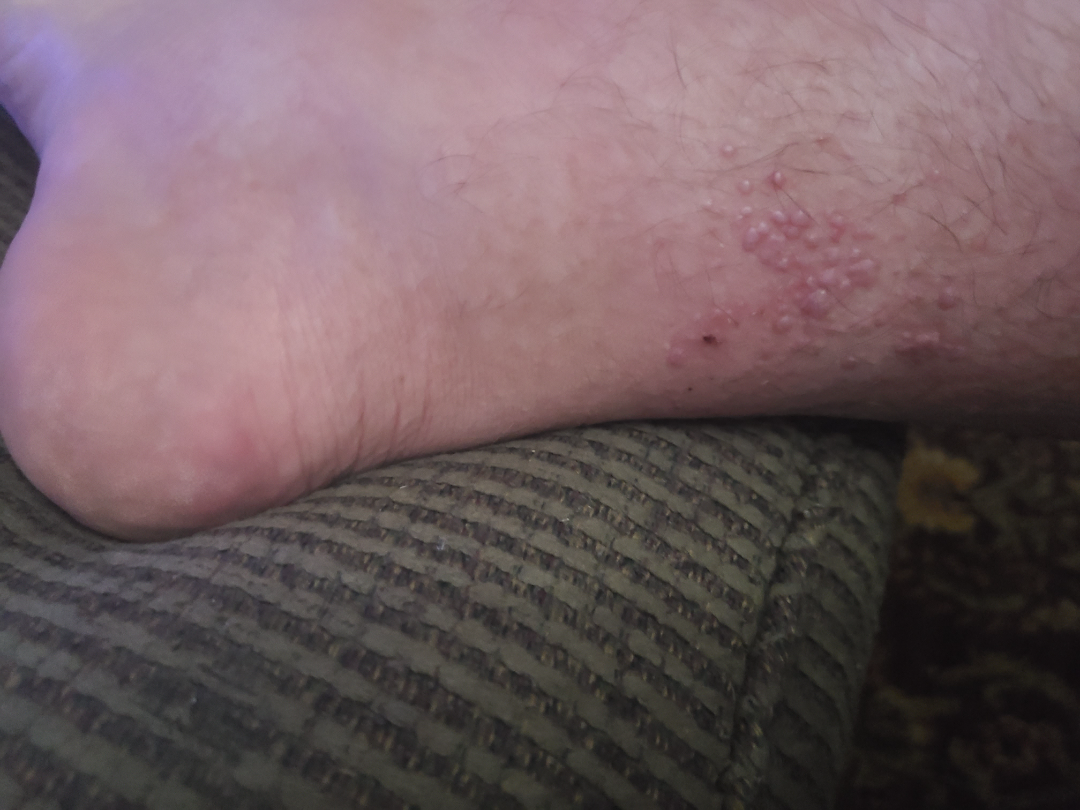The contributor is 50–59, male. This image was taken at a distance. On remote dermatologist review: the leading consideration is Molluscum Contagiosum; also raised was Verruca vulgaris; less likely is Calcinosis cutis.